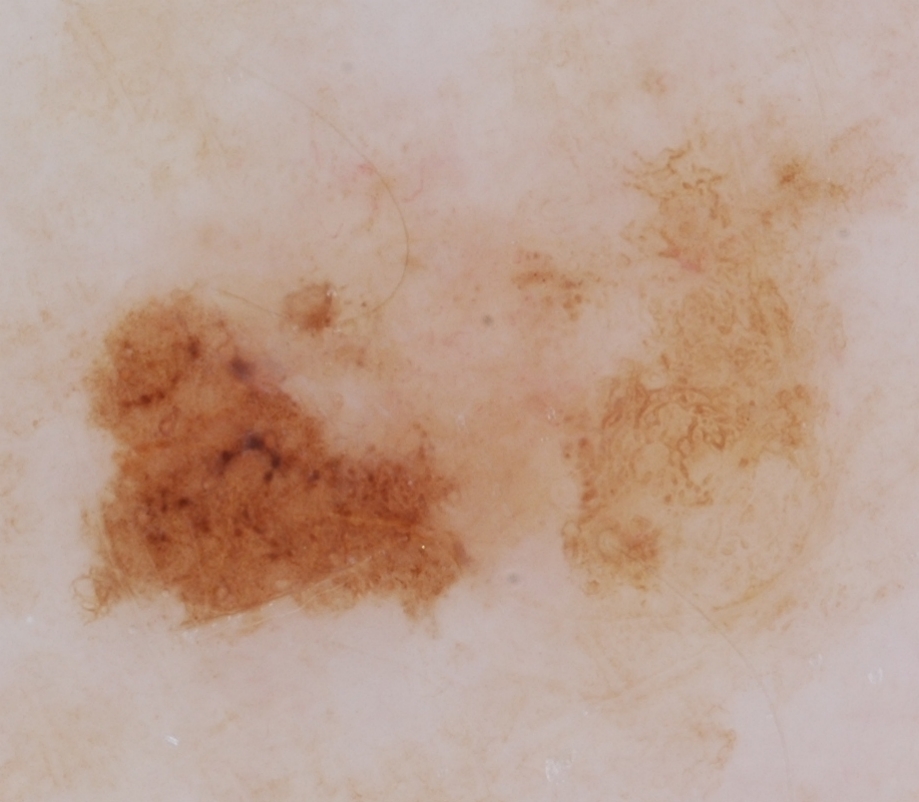Case summary:
- modality — dermoscopic image
- features — globules; absent: milia-like cysts, streaks, negative network, and pigment network
- lesion bbox — 32, 105, 891, 655
- impression — a melanoma